A male patient 83 years of age · the patient says their skin reddens with sun exposure · a skin lesion imaged with a dermatoscope · referred for assessment of suspected Bowen's disease:
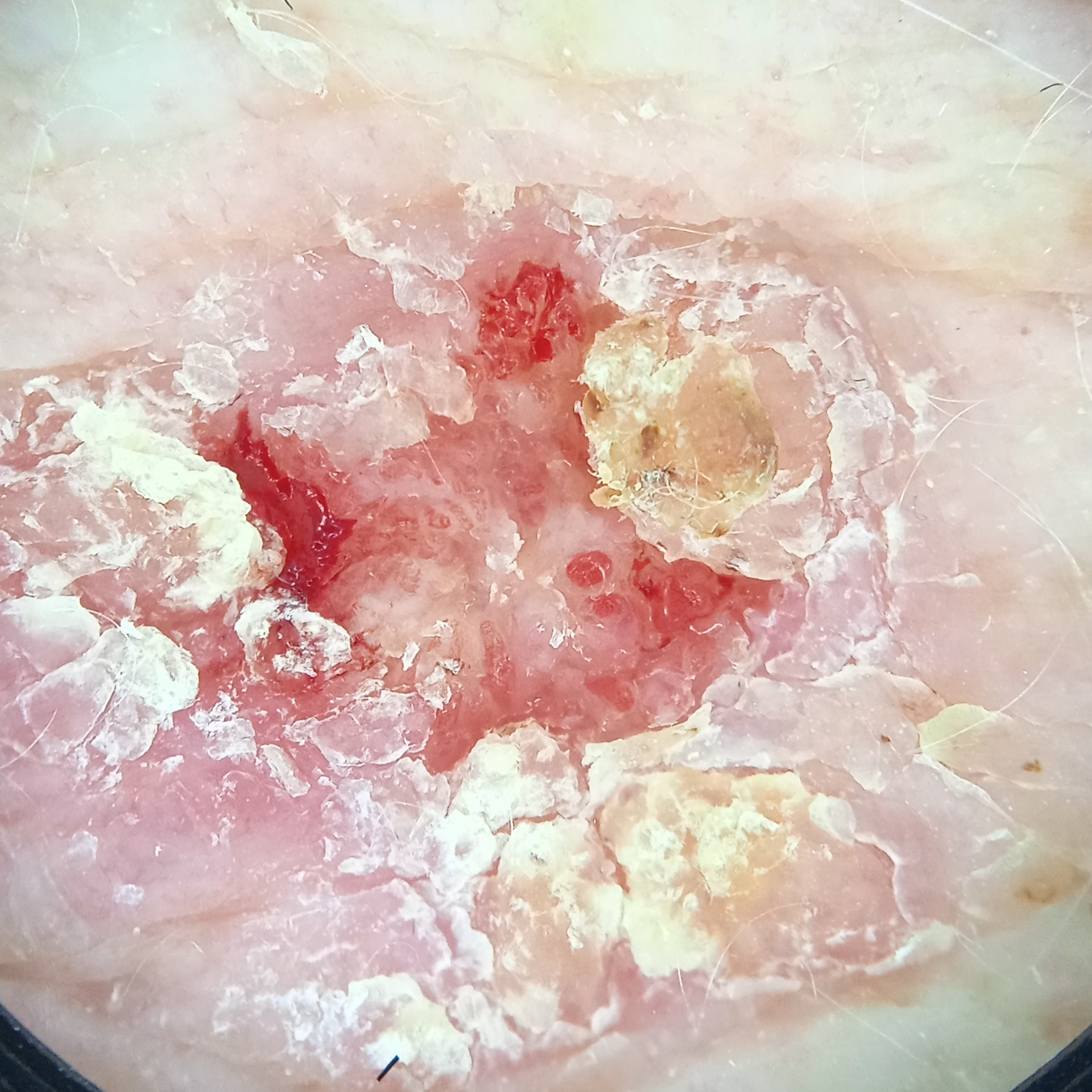anatomic site — the torso
size — 14.5 mm
assessment — squamous cell carcinoma (dermatologist consensus)